The photo was captured at a distance; male contributor, age 18–29:
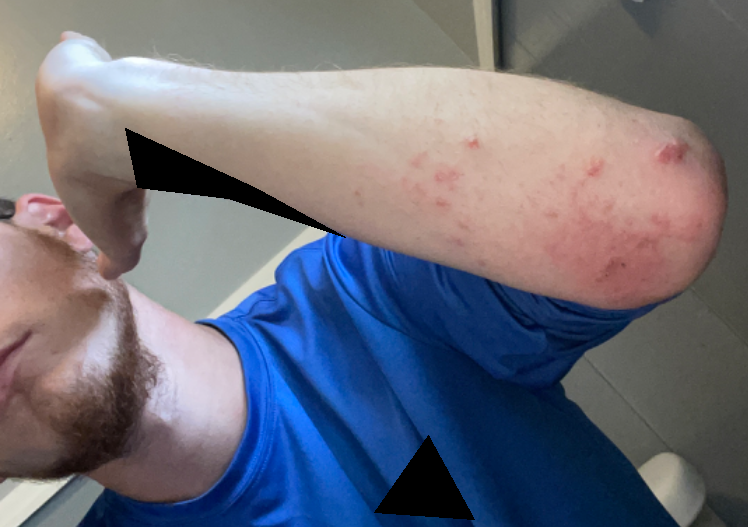assessment = ungradable on photographic review
described texture = raised or bumpy and fluid-filled
patient-reported symptoms = burning, itching and enlargement
patient describes the issue as = a rash
other reported symptoms = none reported
history = less than one week